A skin lesion imaged with a dermatoscope:
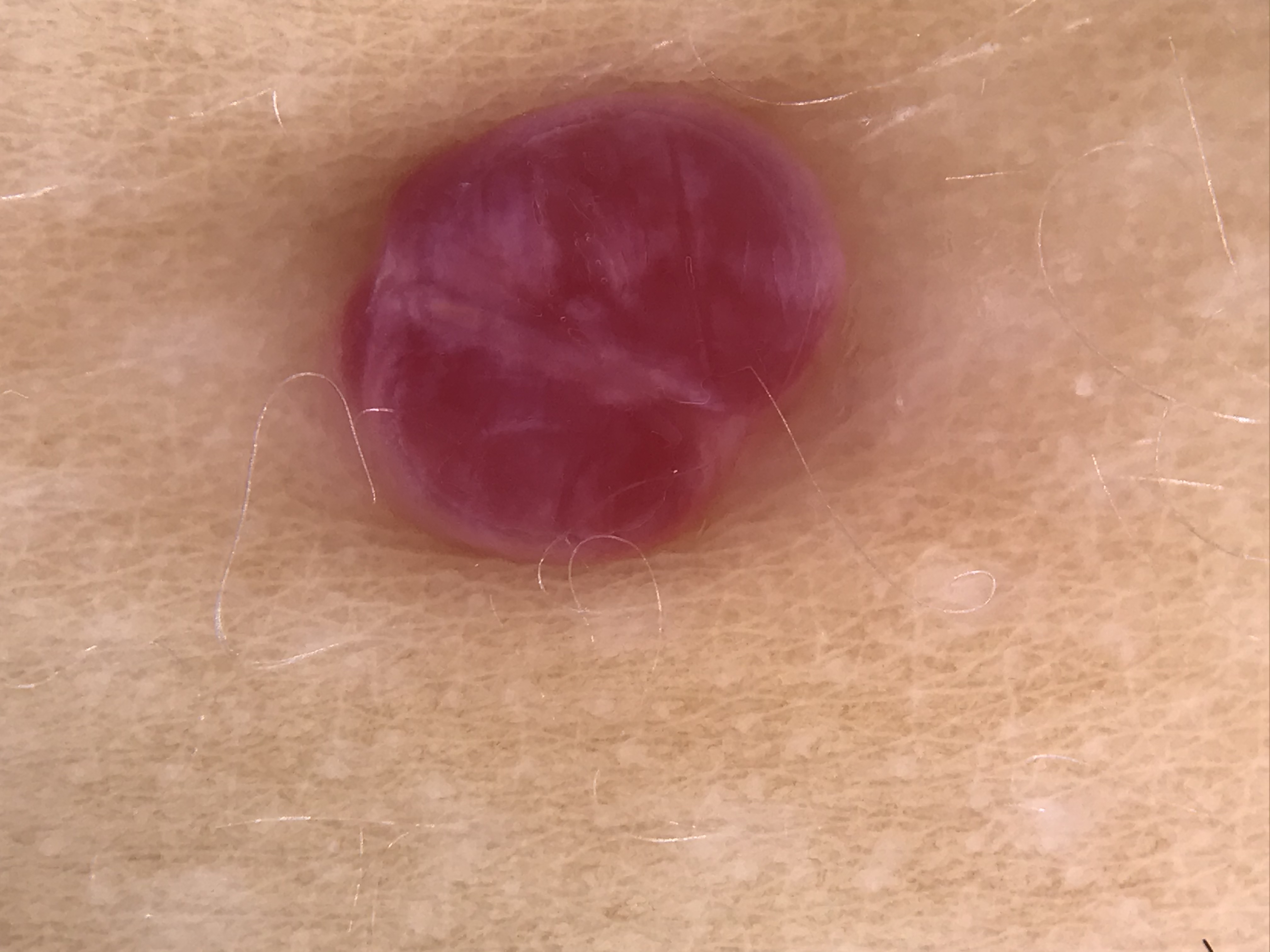diagnosis:
  name: pyogenic granuloma
  code: pg
  malignancy: benign
  super_class: non-melanocytic
  confirmation: expert consensus